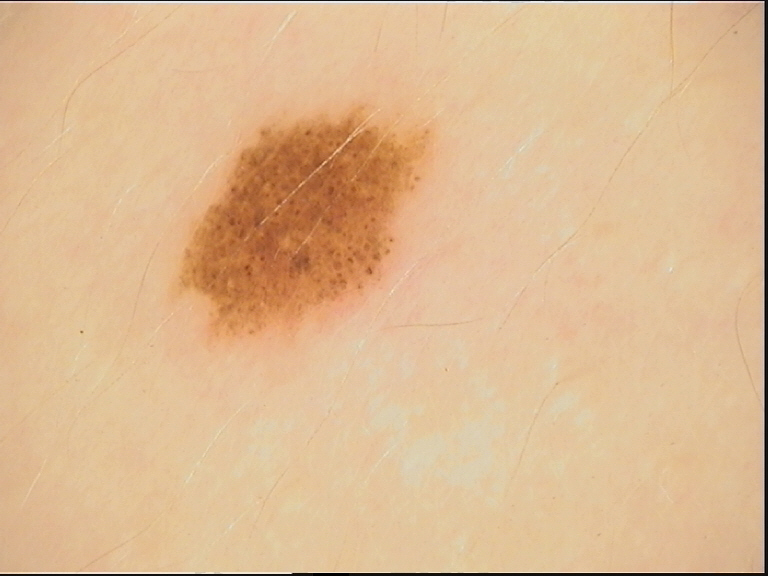• image — dermoscopy
• label — dysplastic junctional nevus (expert consensus)